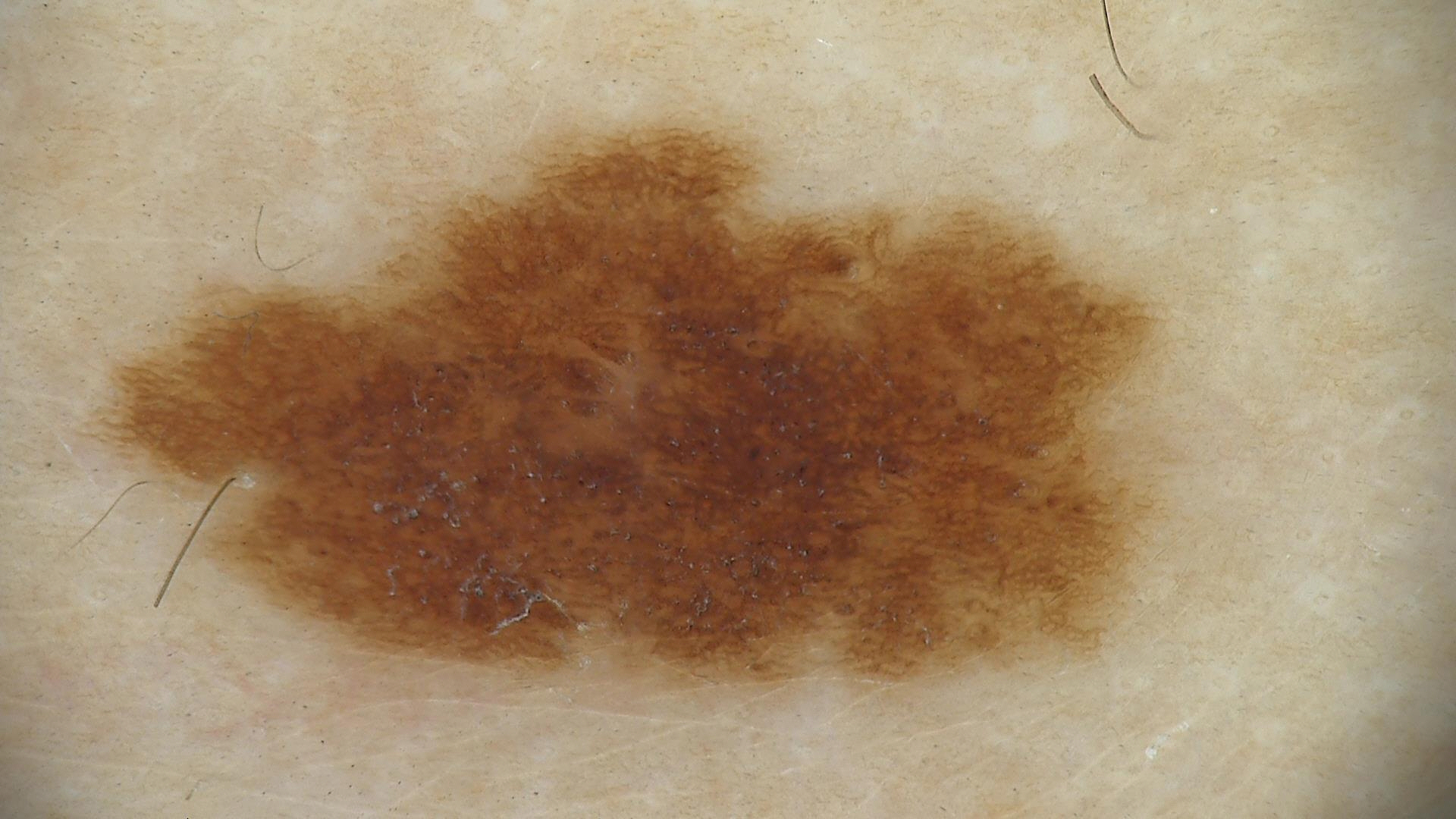Summary: A dermoscopic photograph of a skin lesion. Impression: The diagnosis was a dysplastic junctional nevus.